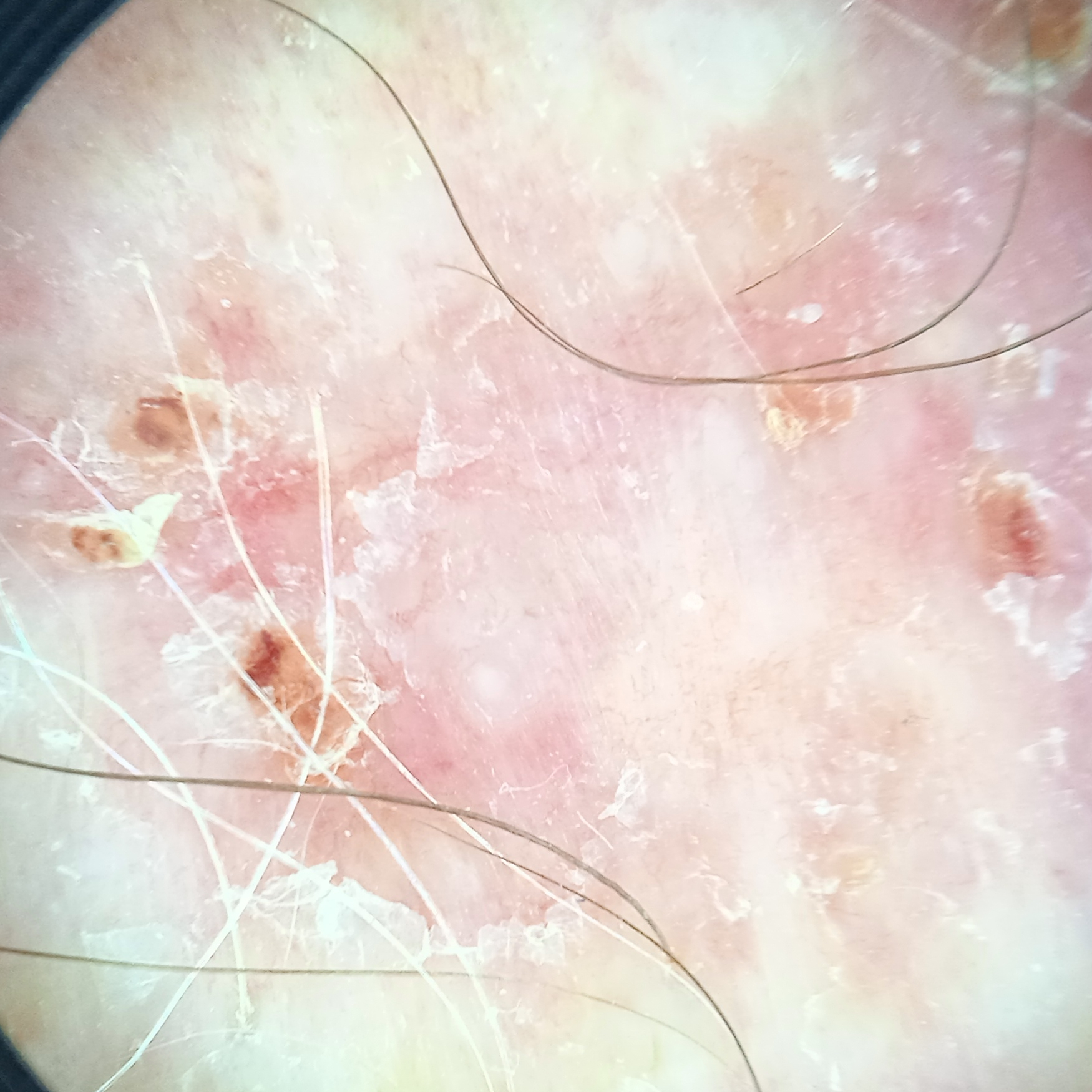referral: clinical suspicion of basal cell carcinoma
subject: male, 67 years of age
anatomic site: the torso
diameter: 19 mm
diagnostic label: basal cell carcinoma (biopsy-proven)